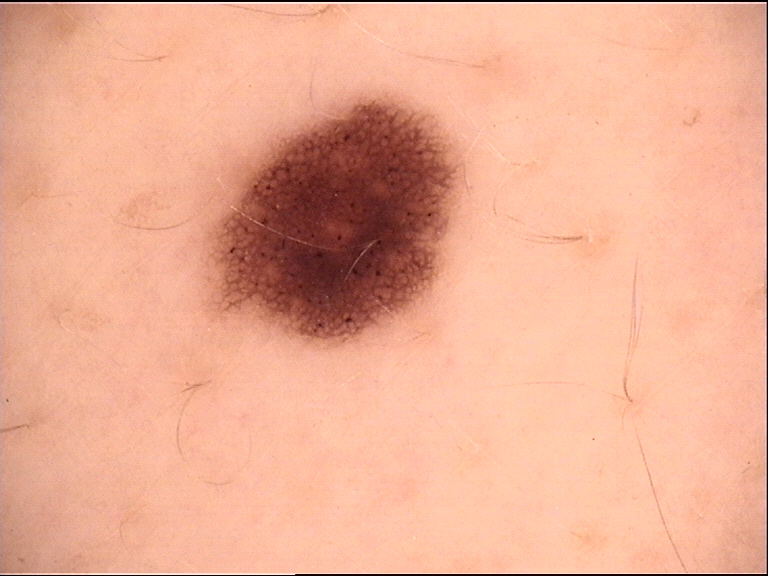A dermoscopic close-up of a skin lesion.
Consistent with a dysplastic junctional nevus.